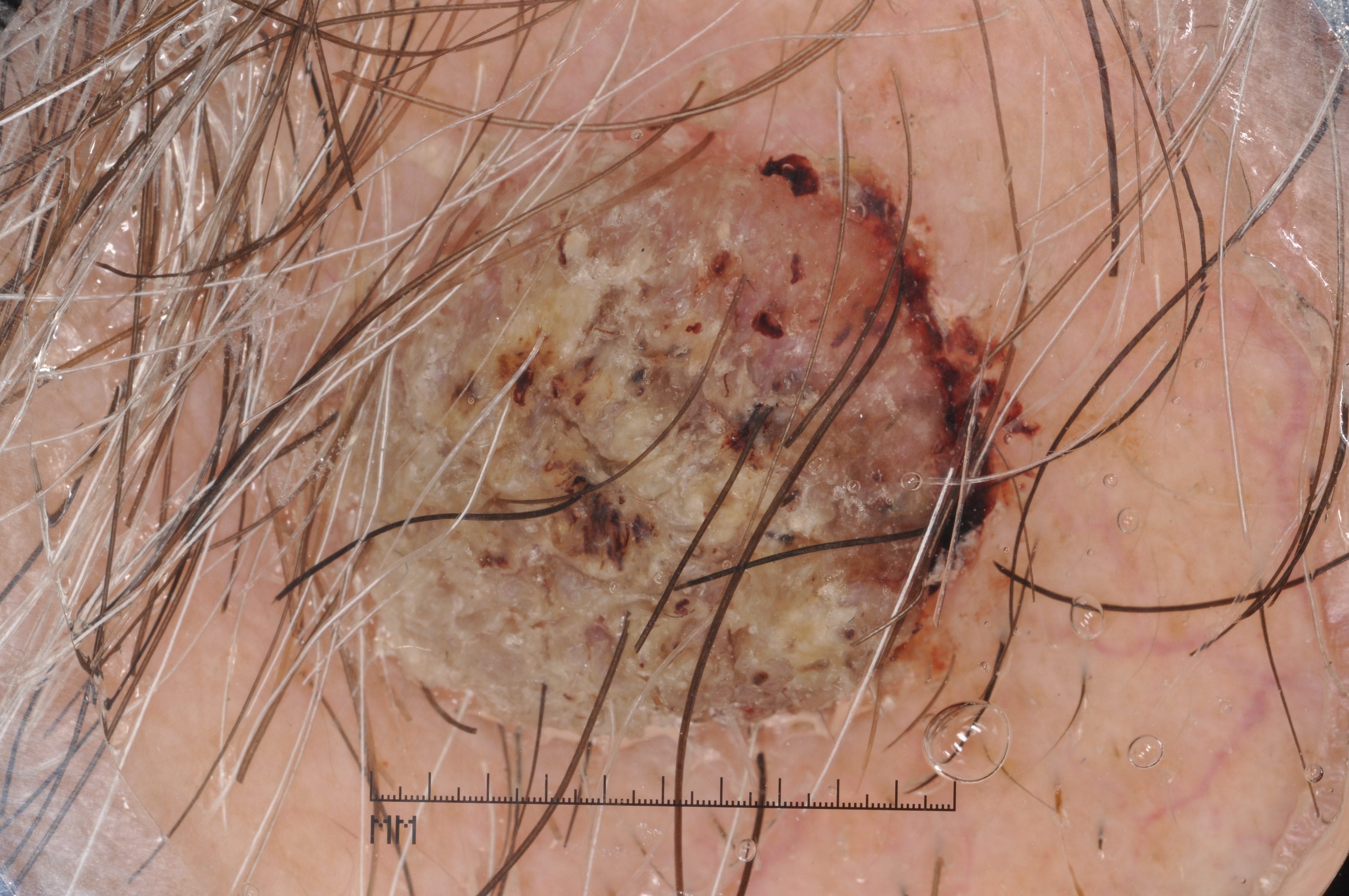imaging = dermatoscopic image of a skin lesion
subject = male, roughly 75 years of age
lesion location = (242, 79, 1051, 783)
lesion size = large
dermoscopic features not present = streaks, pigment network, milia-like cysts, and negative network
impression = a seborrheic keratosis, a non-melanocytic (keratinocytic) lesion